The lesion involves the front of the torso, head or neck, back of the hand, arm and back of the torso · this is a close-up image · the contributor is a male aged 40–49.
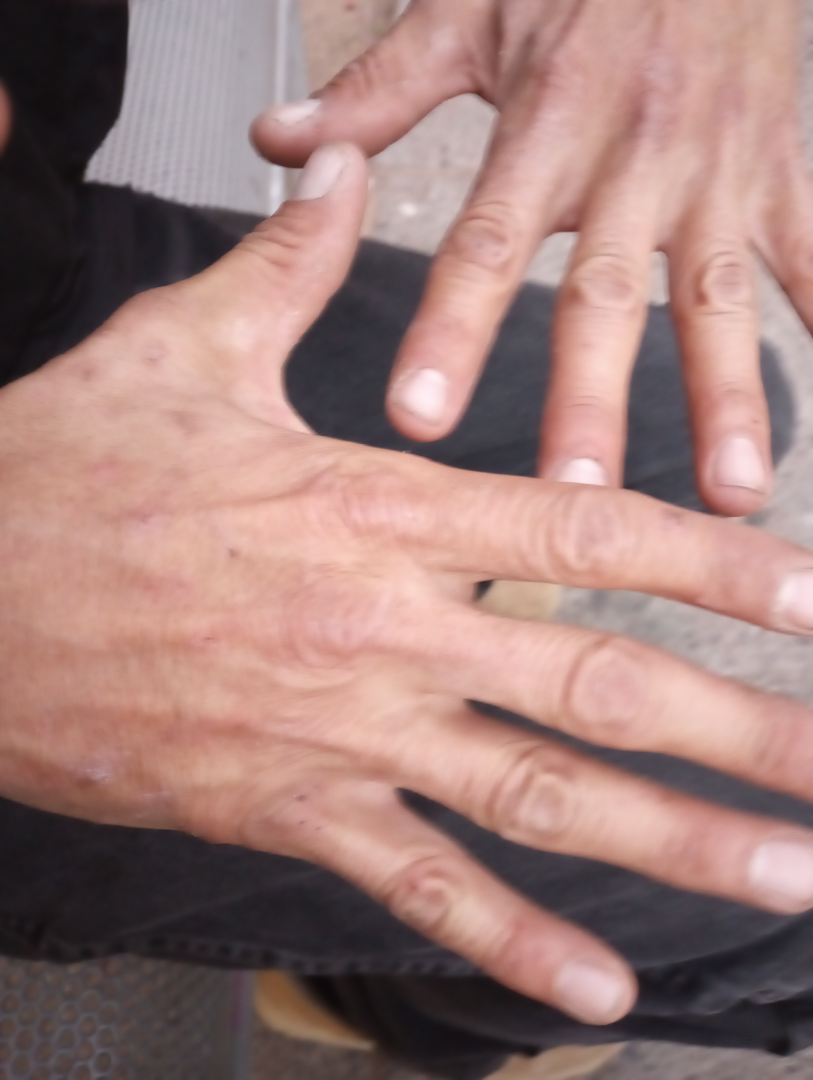assessment: indeterminate from the photograph.